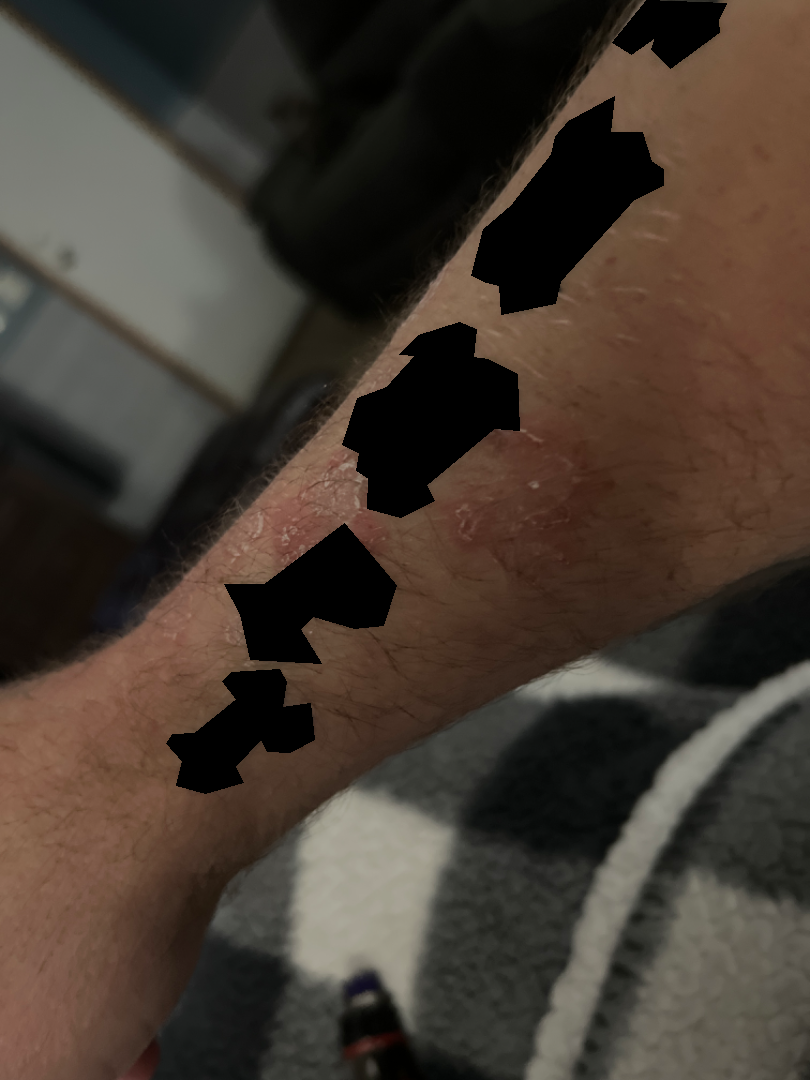The skin findings could not be characterized from the image. Located on the arm. An image taken at an angle. The patient is 40–49, male.